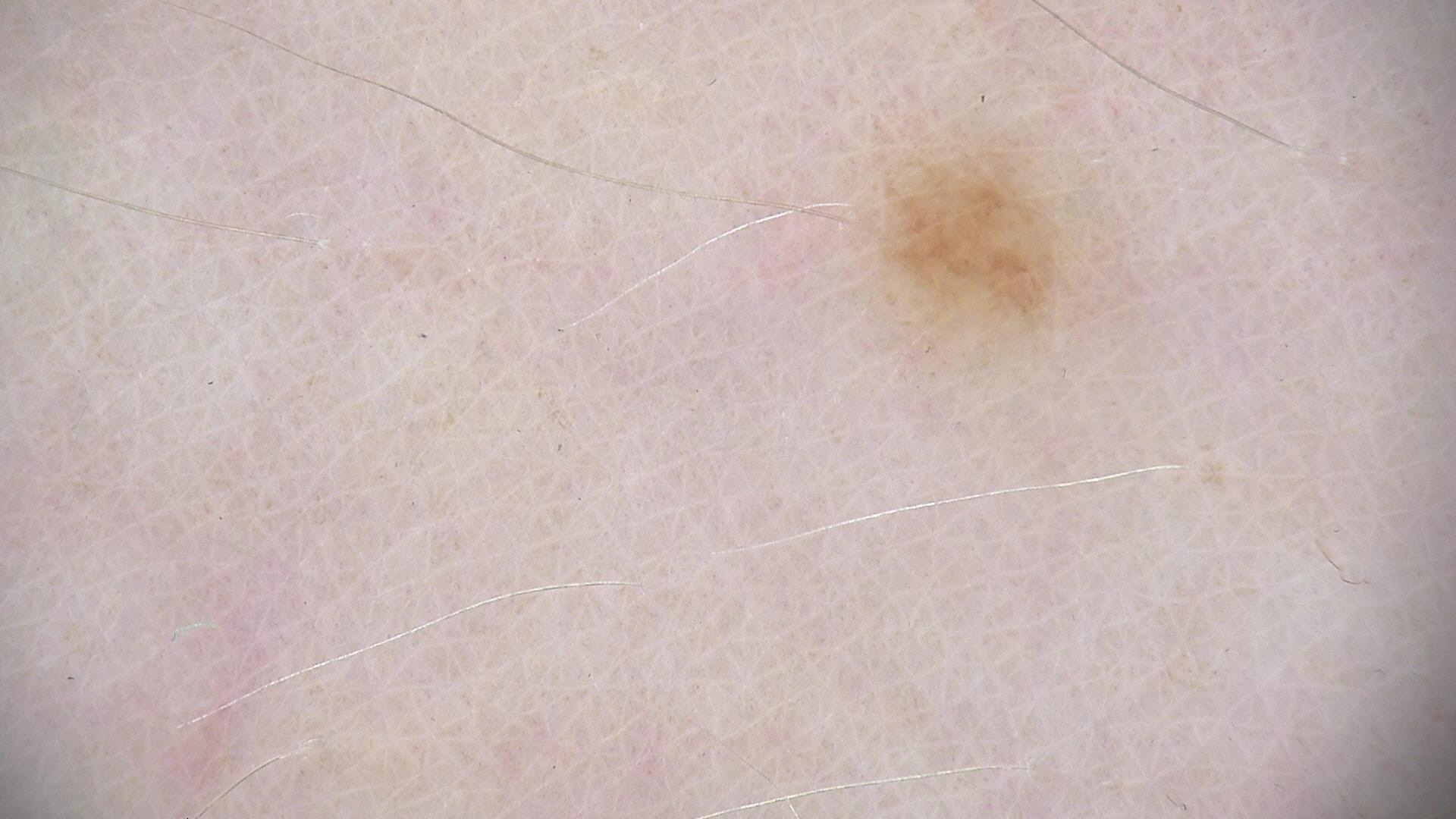modality = dermatoscopy; diagnostic label = dysplastic junctional nevus (expert consensus).